A dermoscopic close-up of a skin lesion.
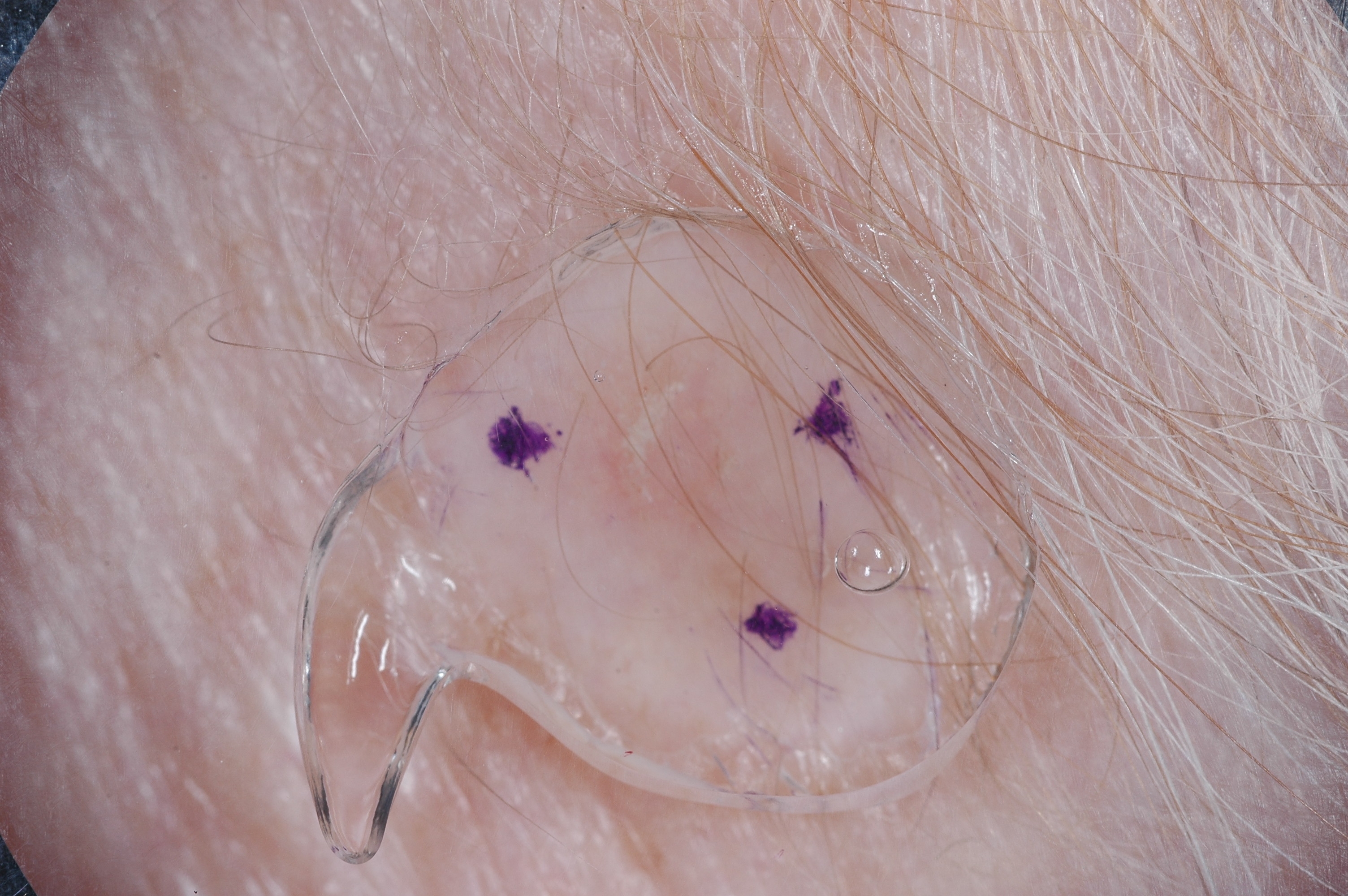Image and clinical context: Dermoscopy demonstrates no negative network, milia-like cysts, pigment network, or streaks. As (left, top, right, bottom), the lesion spans box(580, 330, 849, 654). Conclusion: The clinical diagnosis was a seborrheic keratosis.